Located on the arm · the patient is female · close-up view:
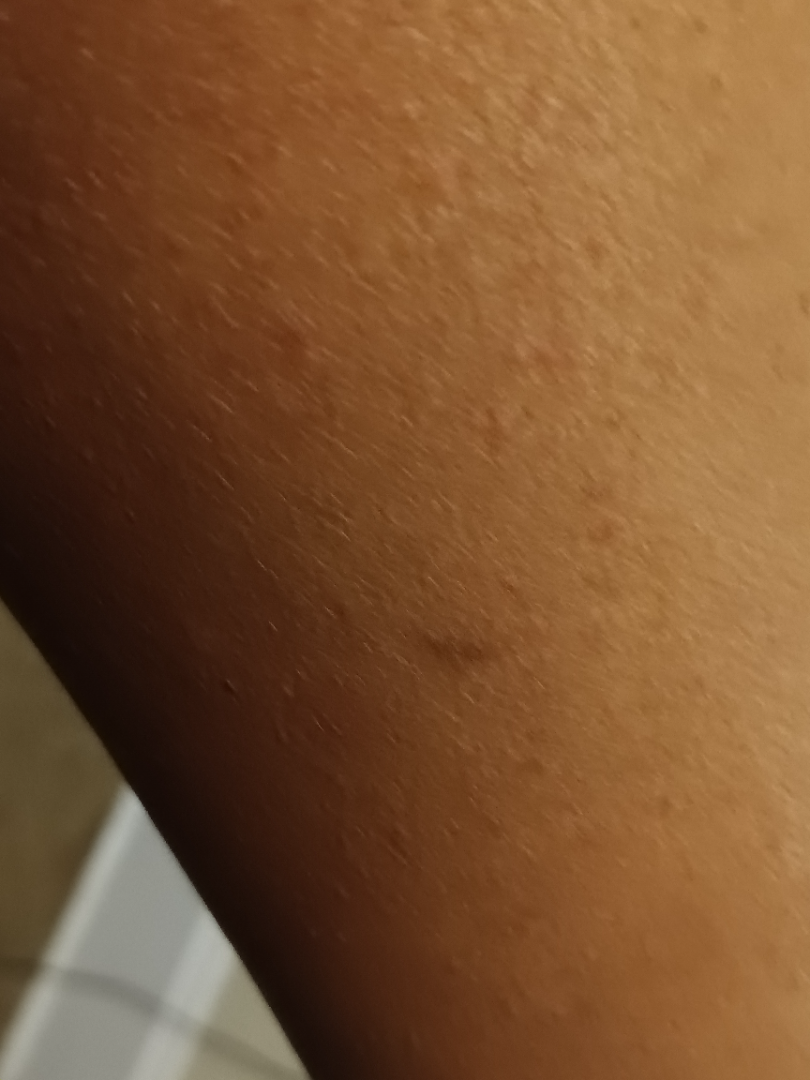Review: Diagnostic features were not clearly distinguishable in this photograph.